A female subject in their early 50s; a smartphone photograph of a skin lesion:
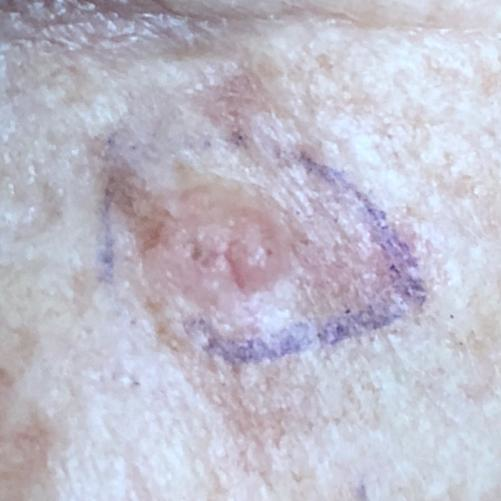<lesion>
<lesion_location>the face</lesion_location>
<symptoms>
<present>elevation</present>
<absent>change in appearance</absent>
</symptoms>
<diagnosis>
<name>basal cell carcinoma</name>
<code>BCC</code>
<malignancy>malignant</malignancy>
<confirmation>histopathology</confirmation>
</diagnosis>
</lesion>